A skin lesion imaged with a dermatoscope.
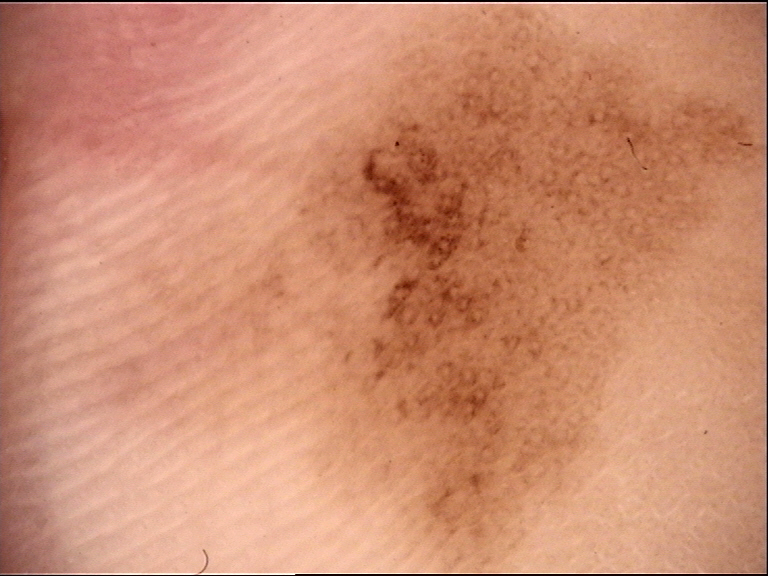<case>
<lesion_type>
<main_class>banal</main_class>
<pattern>junctional</pattern>
</lesion_type>
<diagnosis>
<name>acral junctional nevus</name>
<code>ajb</code>
<malignancy>benign</malignancy>
<super_class>melanocytic</super_class>
<confirmation>expert consensus</confirmation>
</diagnosis>
</case>